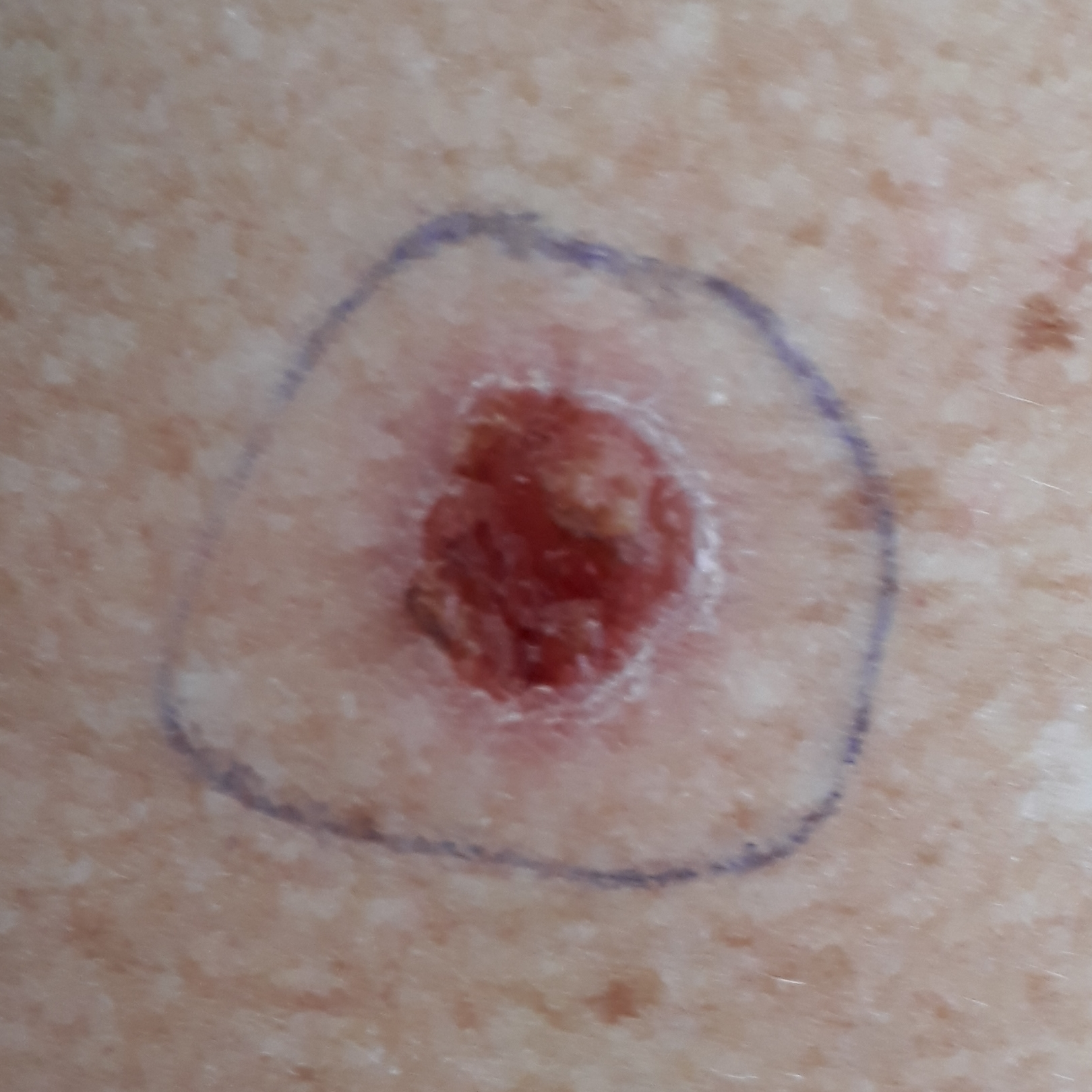| feature | finding |
|---|---|
| exposures | prior malignancy (patient or family), prior skin cancer (patient or family), no tobacco use, no pesticide exposure |
| patient | female, in their late 50s |
| FST | II |
| image type | clinical photo |
| anatomic site | an arm |
| lesion diameter | 10 × 9 mm |
| reported symptoms | bleeding, elevation, itching / no pain |
| diagnostic label | basal cell carcinoma (biopsy-proven) |